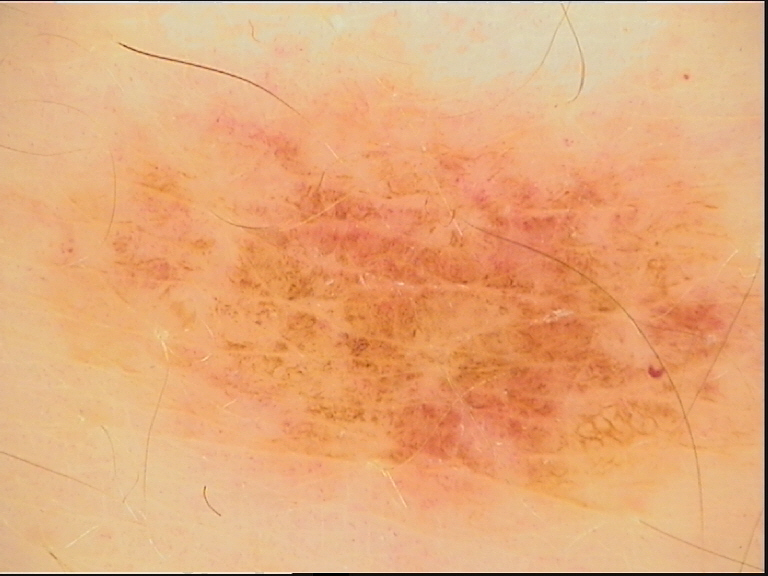| key | value |
|---|---|
| imaging | dermatoscopy |
| subtype | banal |
| diagnosis | compound nevus (expert consensus) |